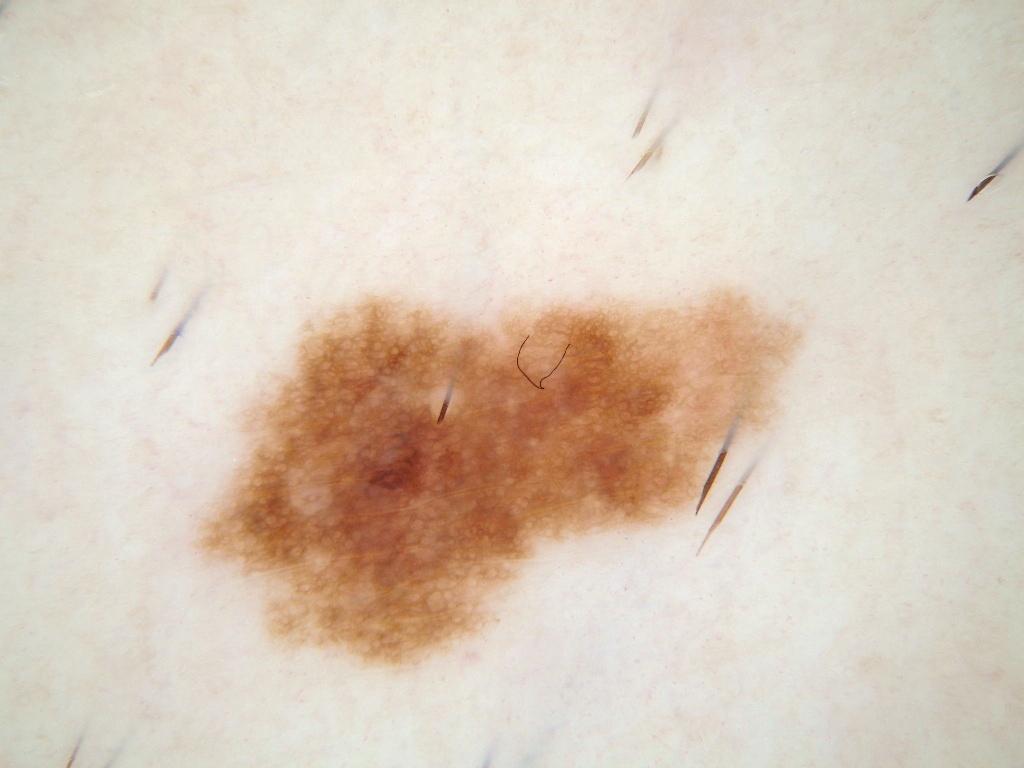modality = dermatoscopic image of a skin lesion | patient = male, about 35 years old | lesion bbox = [192, 285, 803, 671] | size = moderate | dermoscopic findings = pigment network; absent: globules, streaks, milia-like cysts, and negative network | assessment = a melanocytic nevus.